A dermoscopy image of a single skin lesion.
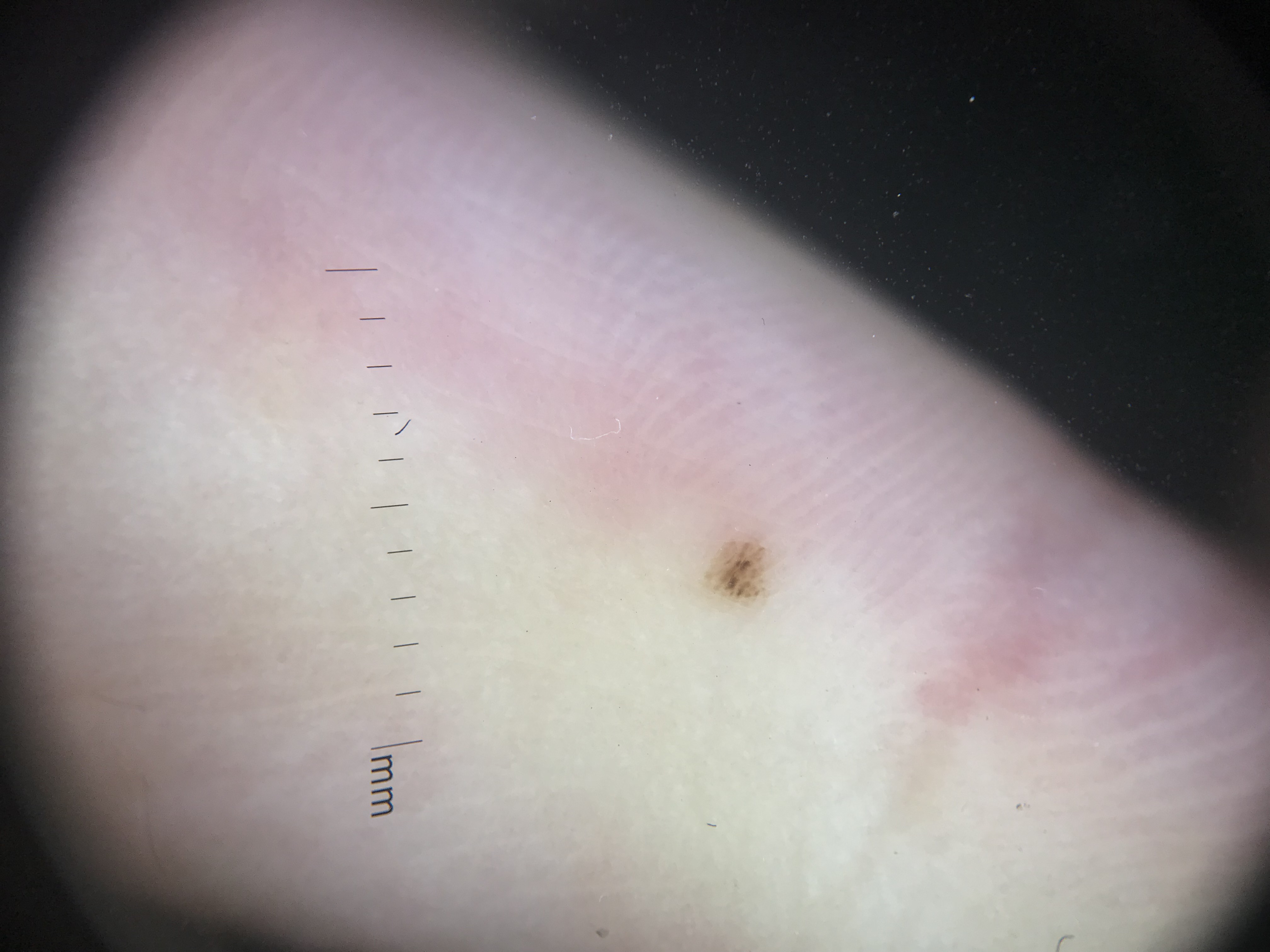diagnostic label: acral junctional nevus (expert consensus).